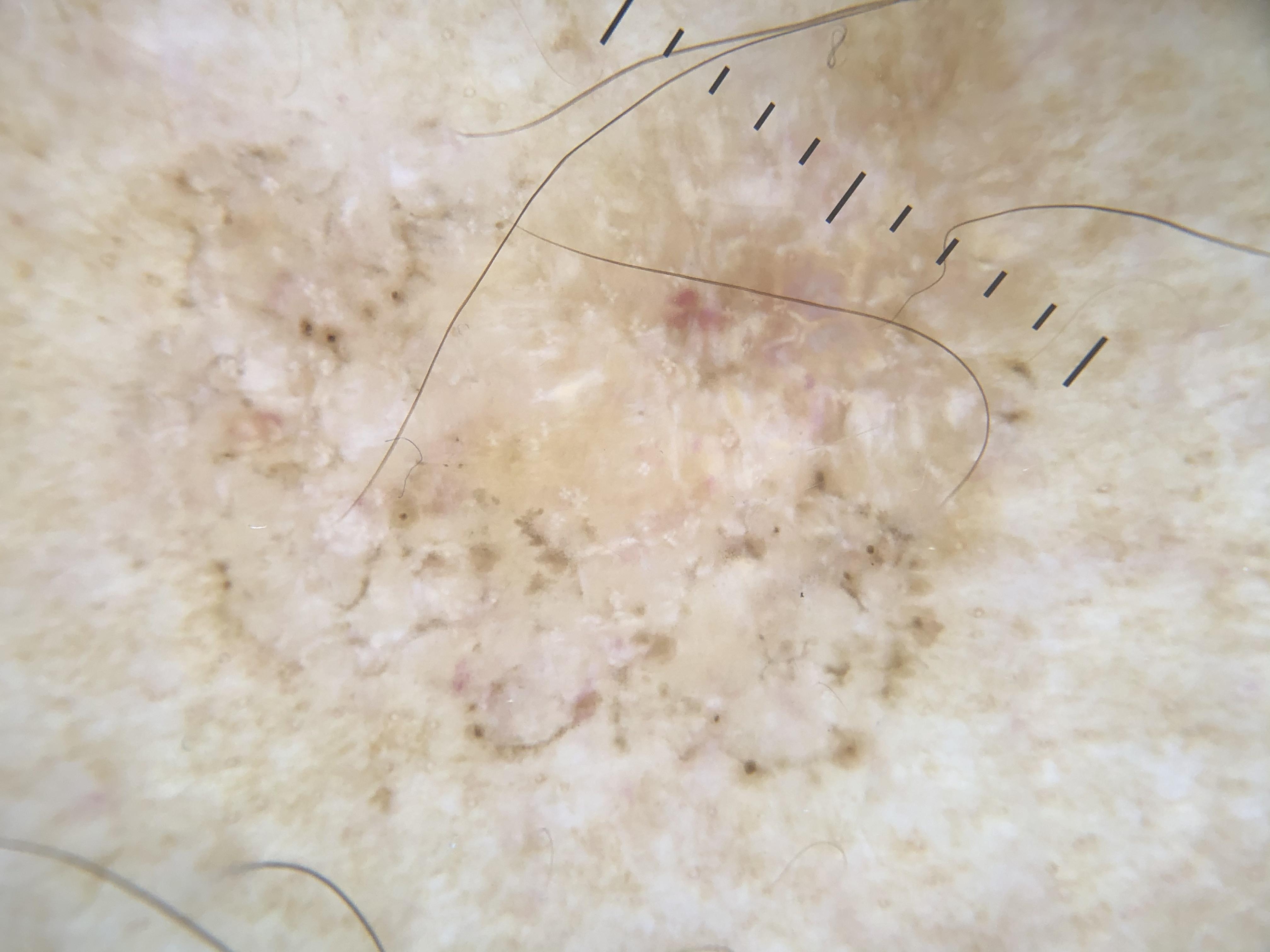| key | value |
|---|---|
| pathology | Basal cell carcinoma (biopsy-proven) |